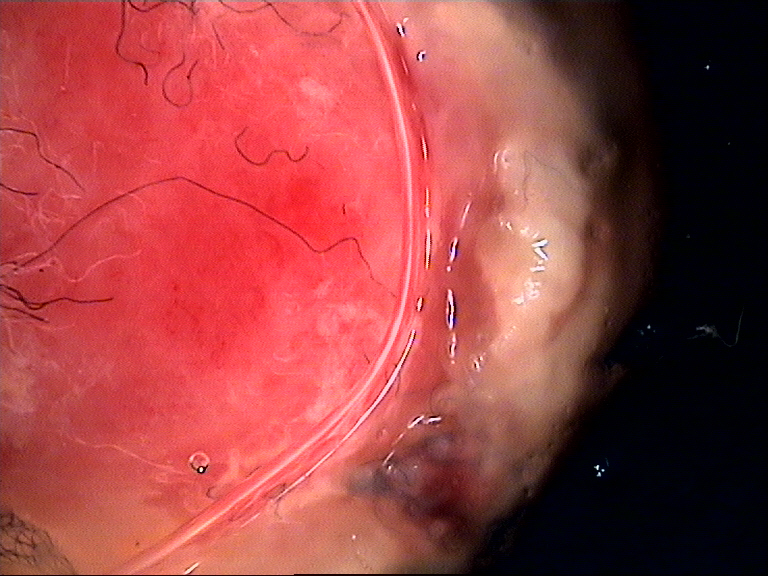Biopsy-confirmed as an acral nodular melanoma.